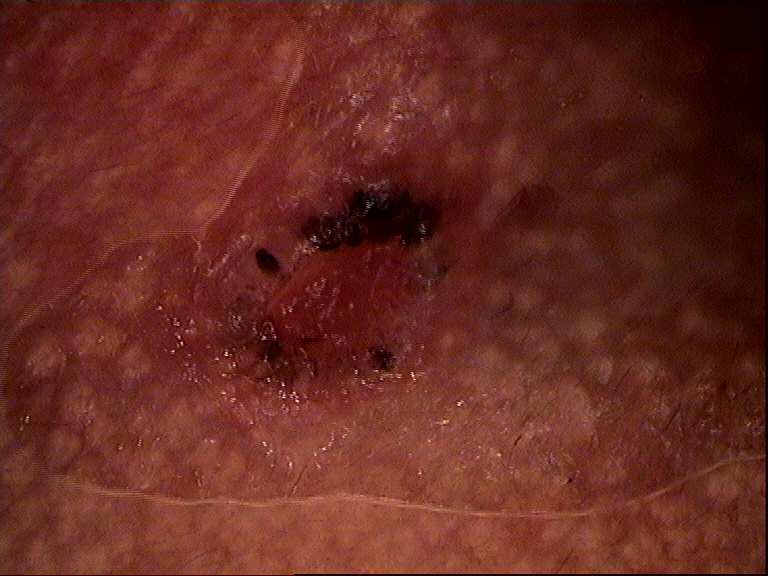Q: What did the workup show?
A: basal cell carcinoma (biopsy-proven)